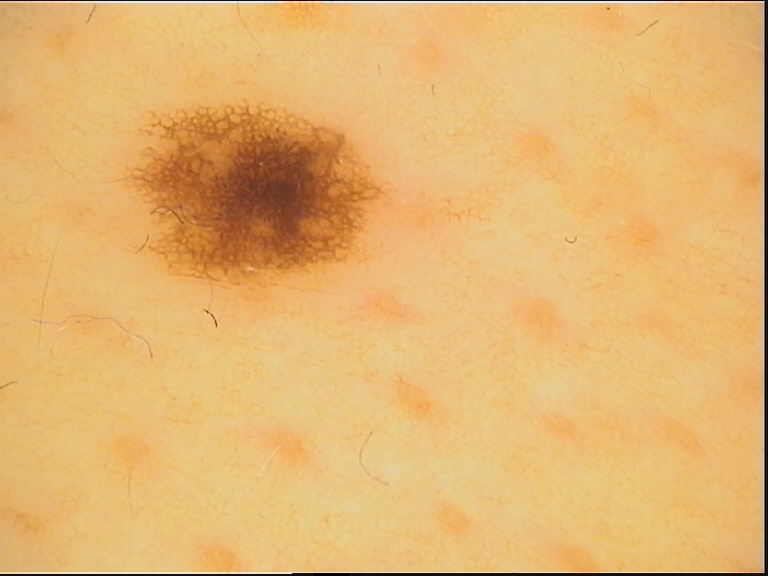class: junctional nevus (expert consensus).